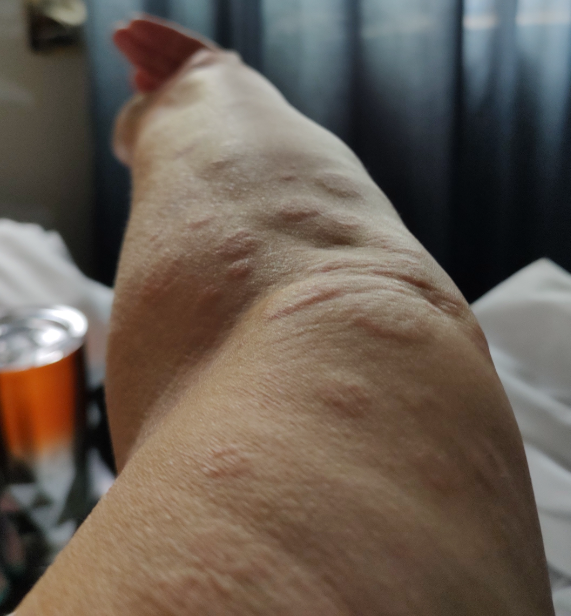{"patient_category": "skin that appeared healthy to them", "duration": "one to four weeks", "shot_type": "at a distance", "skin_tone": {"fitzpatrick": "III", "fitzpatrick_source": "self_reported", "monk_skin_tone": [2, 3]}, "body_site": ["arm", "front of the torso"], "texture": "raised or bumpy", "systemic_symptoms": ["shortness of breath", "fatigue"], "symptoms": ["itching", "enlargement"], "patient": "female, age 50–59", "differential": {"leading": ["Cutaneous metastasis"], "considered": ["Urticaria", "Pseudolymphoma"]}}